Located on the arm, head or neck and front of the torso. This is a close-up image:
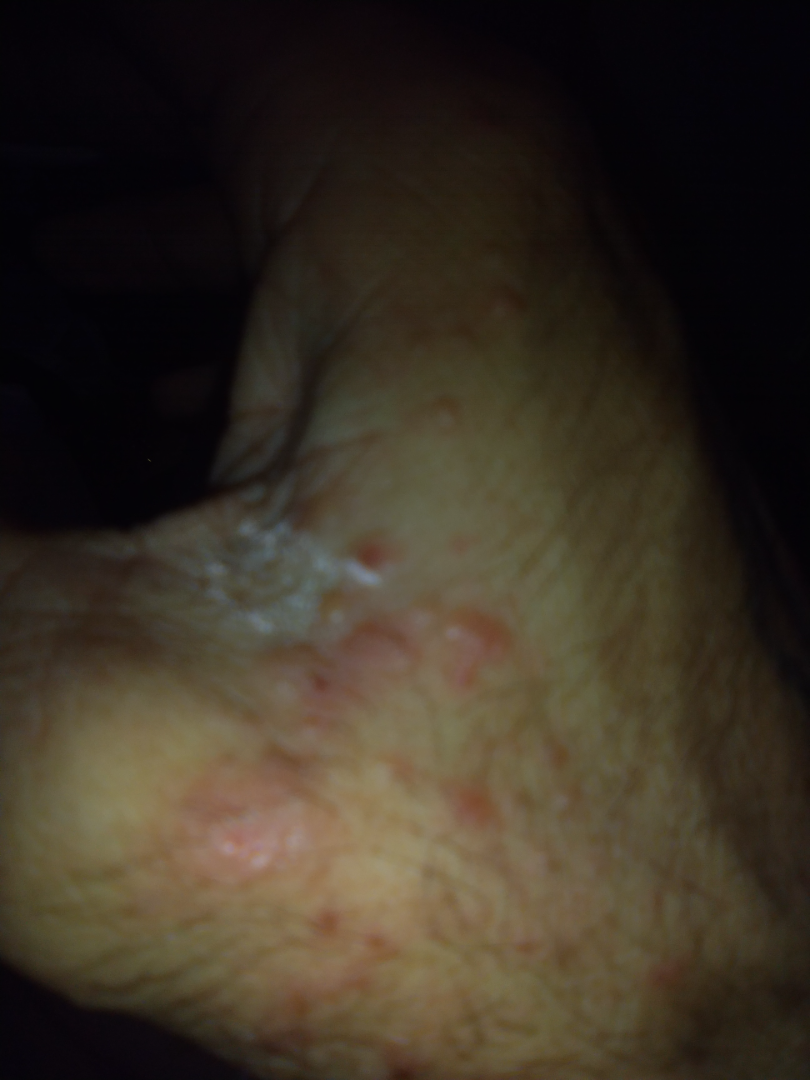{
  "assessment": "could not be assessed",
  "symptoms": [
    "enlargement",
    "bothersome appearance"
  ]
}